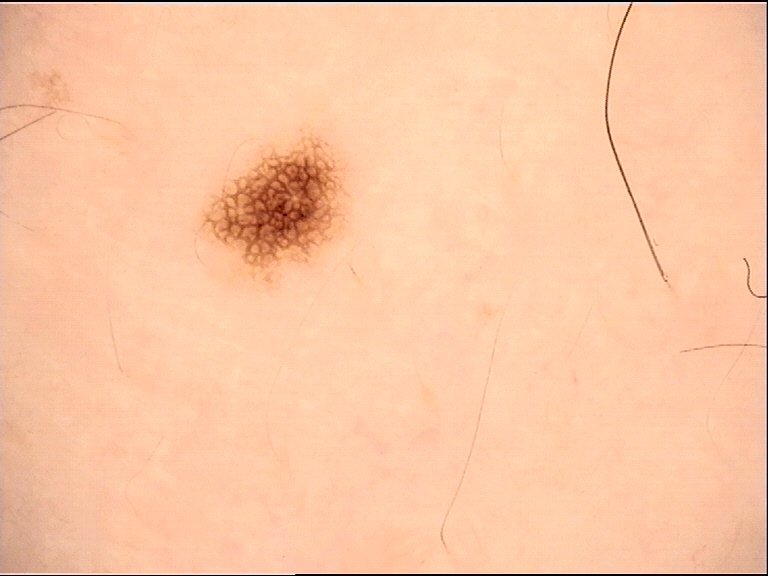image type: dermoscopy | label: dysplastic junctional nevus (expert consensus).